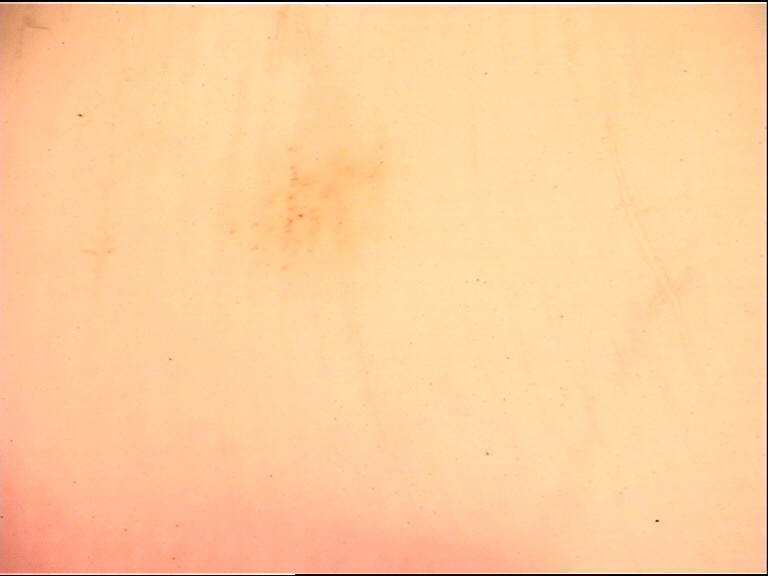* imaging — dermoscopy
* subtype — banal
* assessment — acral junctional nevus (expert consensus)